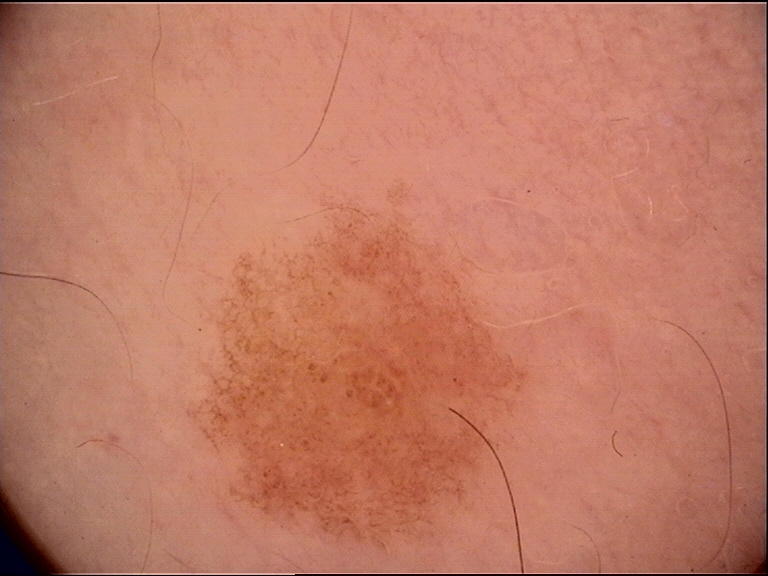Dermoscopy of a skin lesion. Labeled as a dysplastic junctional nevus.